A clinical photograph of a skin lesion; a patient 41 years old.
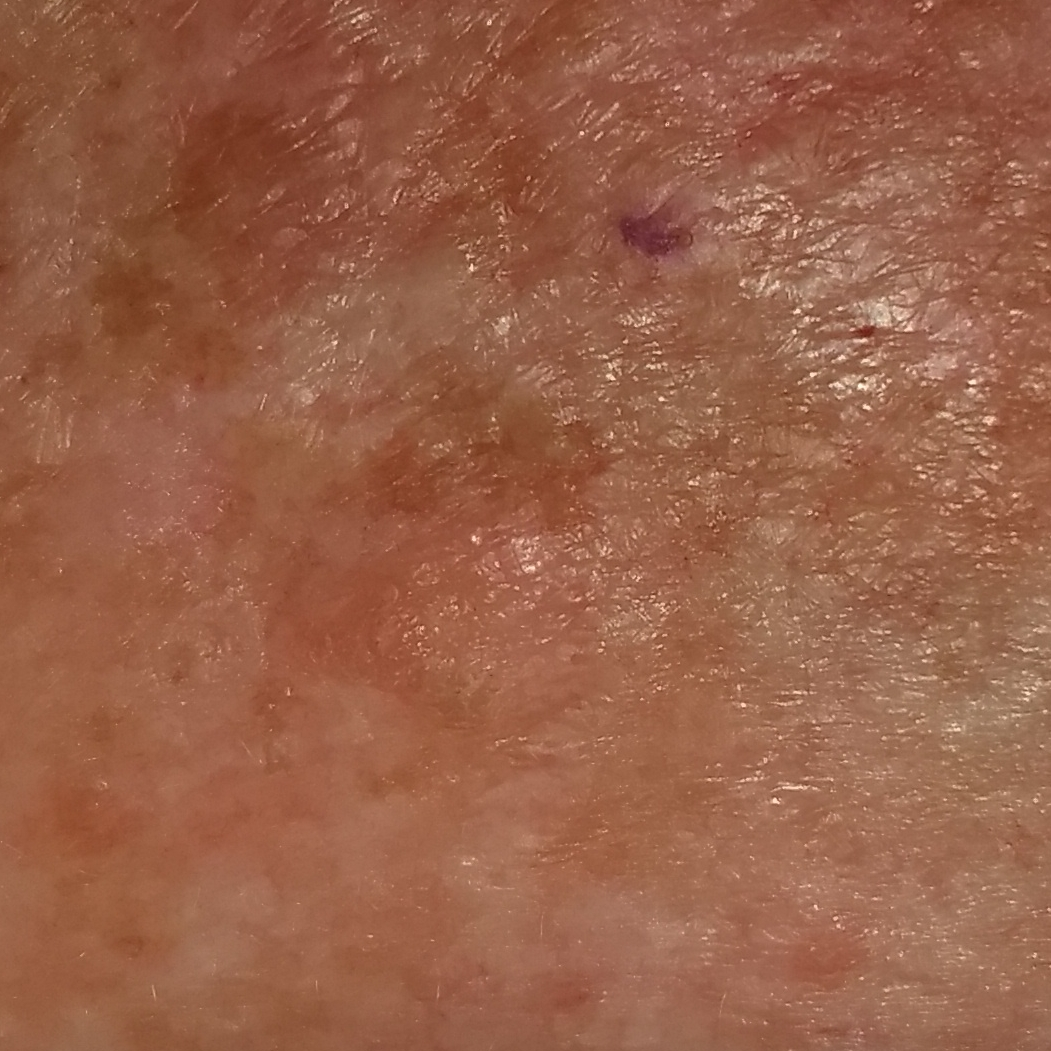site = the chest; reported symptoms = pain, itching; diagnostic label = actinic keratosis (clinical consensus).